The contributor is 18–29, male. The affected area is the front of the torso, leg and back of the torso. This is a close-up image.
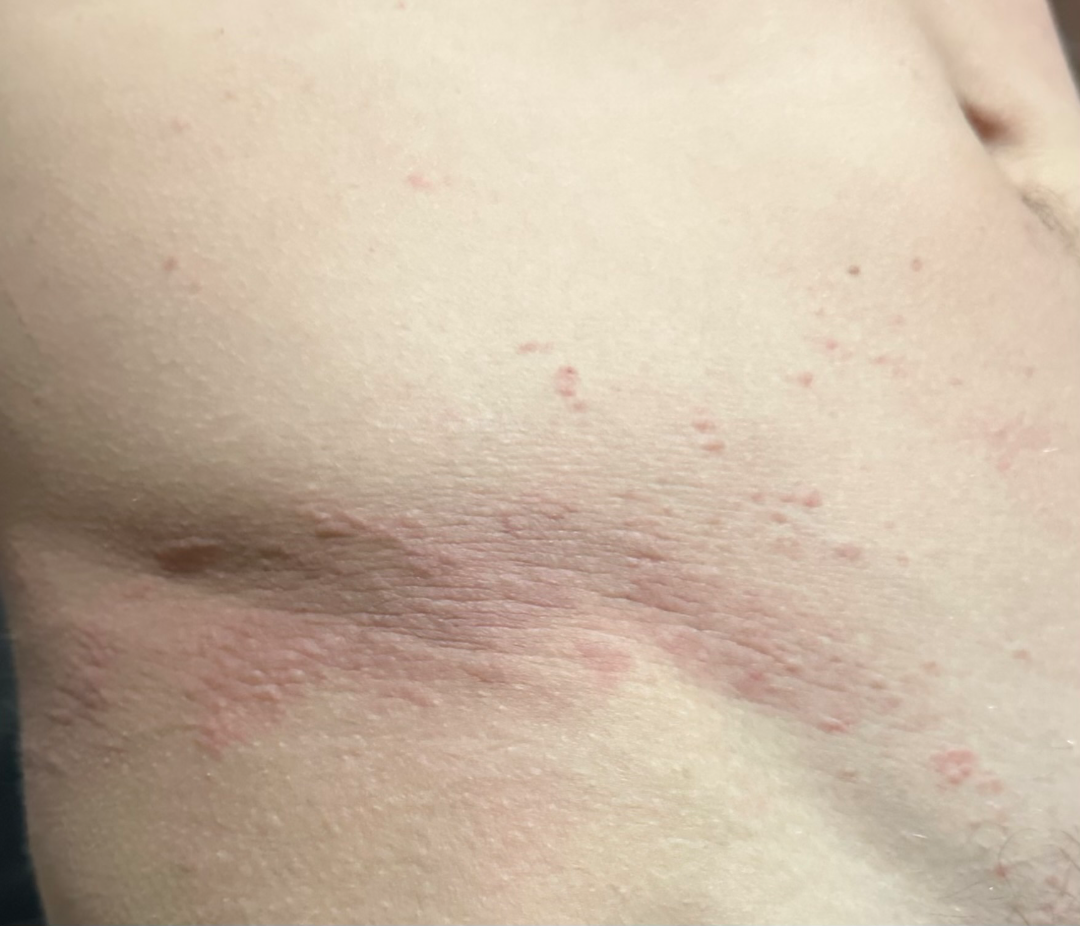The case was difficult to assess from the available photograph.